Female contributor, age 50–59. The lesion is associated with enlargement, bothersome appearance and itching. The photo was captured at a distance. The affected area is the palm and back of the hand.
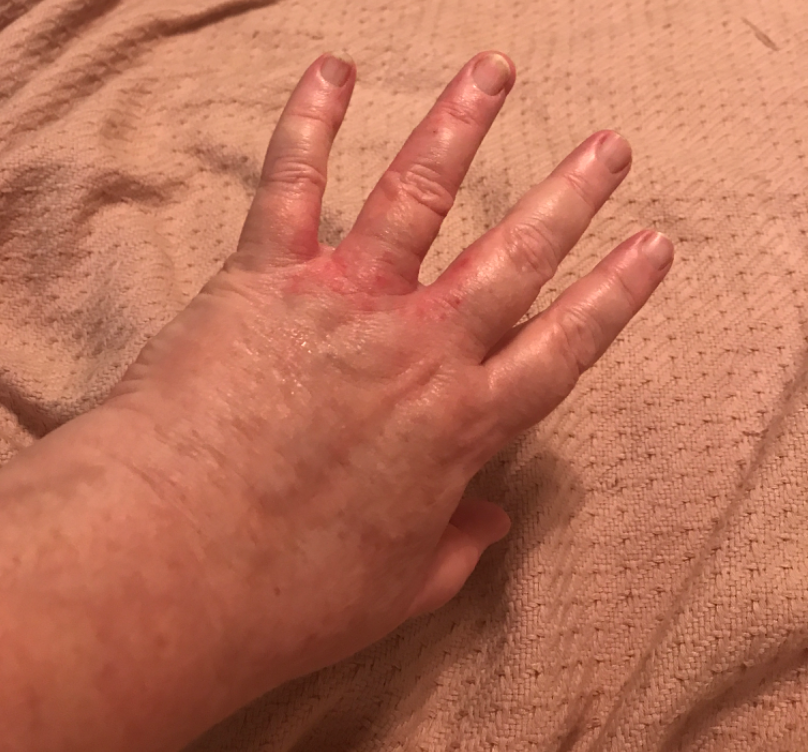Impression: The favored diagnosis is Eczema; an alternative is Allergic Contact Dermatitis; a more distant consideration is Scabies; less likely is Tinea; less probable is Irritant Contact Dermatitis.